Located on the top or side of the foot · male subject, age 30–39 · close-up view.
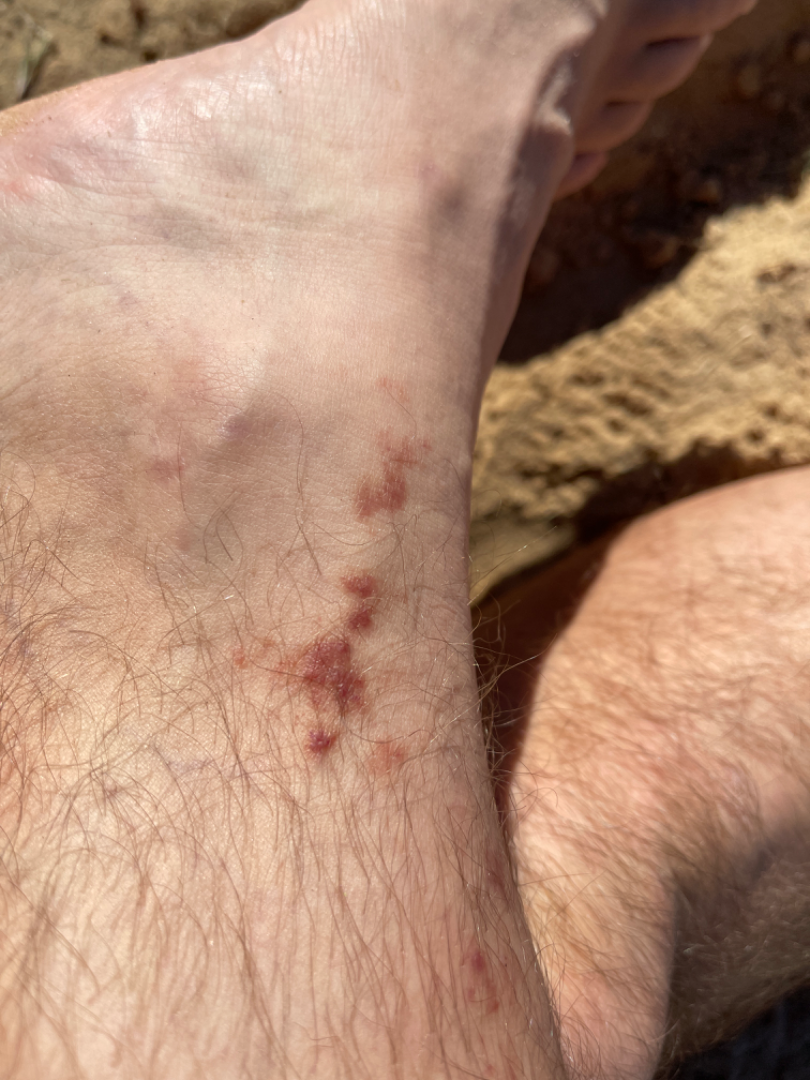On photographic review: Lichen planus/lichenoid eruption (possible); Pigmented purpuric eruption (possible); Kaposi's sarcoma of skin (possible).